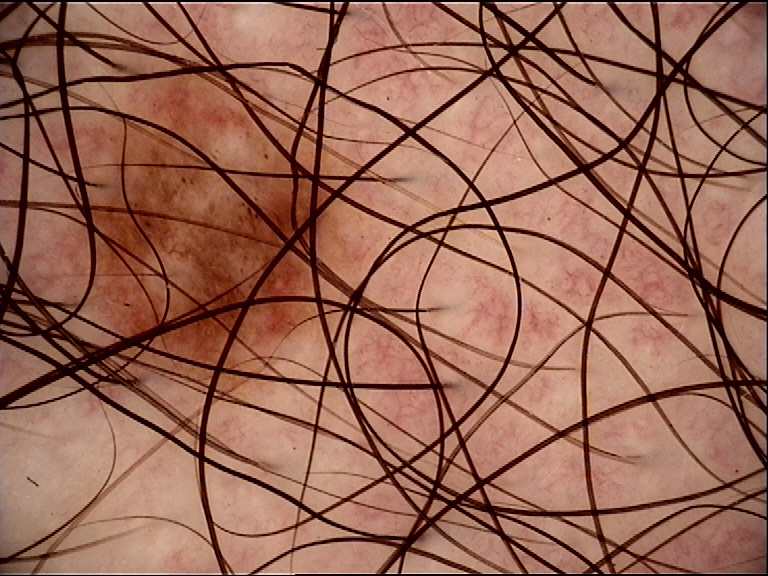image: dermoscopy
diagnosis:
  name: dysplastic junctional nevus
  code: jd
  malignancy: benign
  super_class: melanocytic
  confirmation: expert consensus